The leg is involved. The photo was captured at a distance. The subject is a male aged 18–29 — 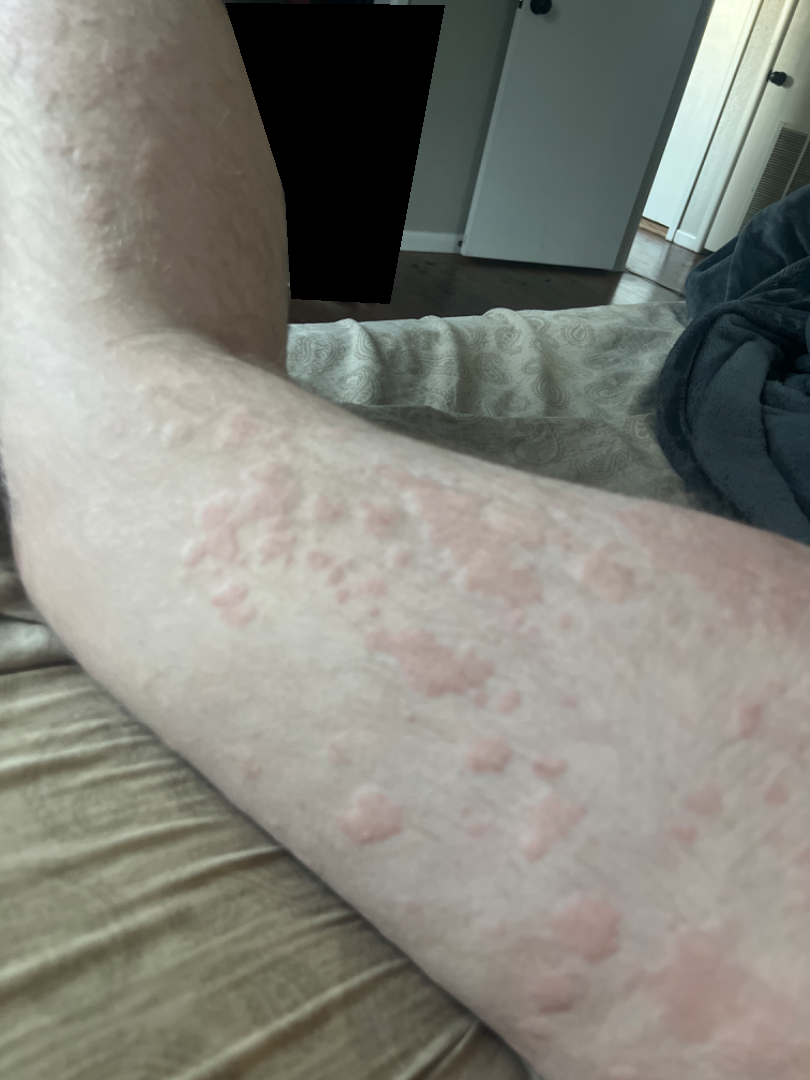{
  "patient_category": "skin that appeared healthy to them",
  "duration": "about one day",
  "skin_tone": {
    "fitzpatrick": "III",
    "monk_skin_tone": [
      1,
      2
    ]
  },
  "symptoms": [
    "itching",
    "enlargement"
  ],
  "texture": [
    "flat",
    "raised or bumpy"
  ],
  "differential": {
    "leading": [
      "Urticaria"
    ]
  }
}